The photograph was taken at an angle. The patient notes bothersome appearance and itching. The condition has been present for less than one week. Located on the arm and leg. The lesion is described as raised or bumpy.
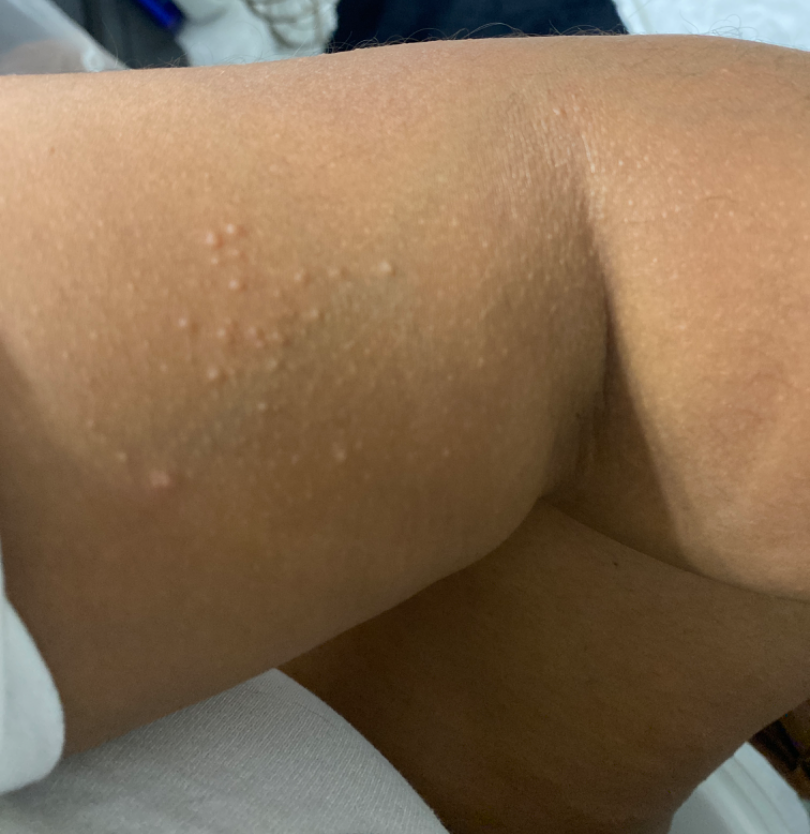* clinical impression — reviewed remotely by three dermatologists: most consistent with Folliculitis; also consider Keratosis pilaris